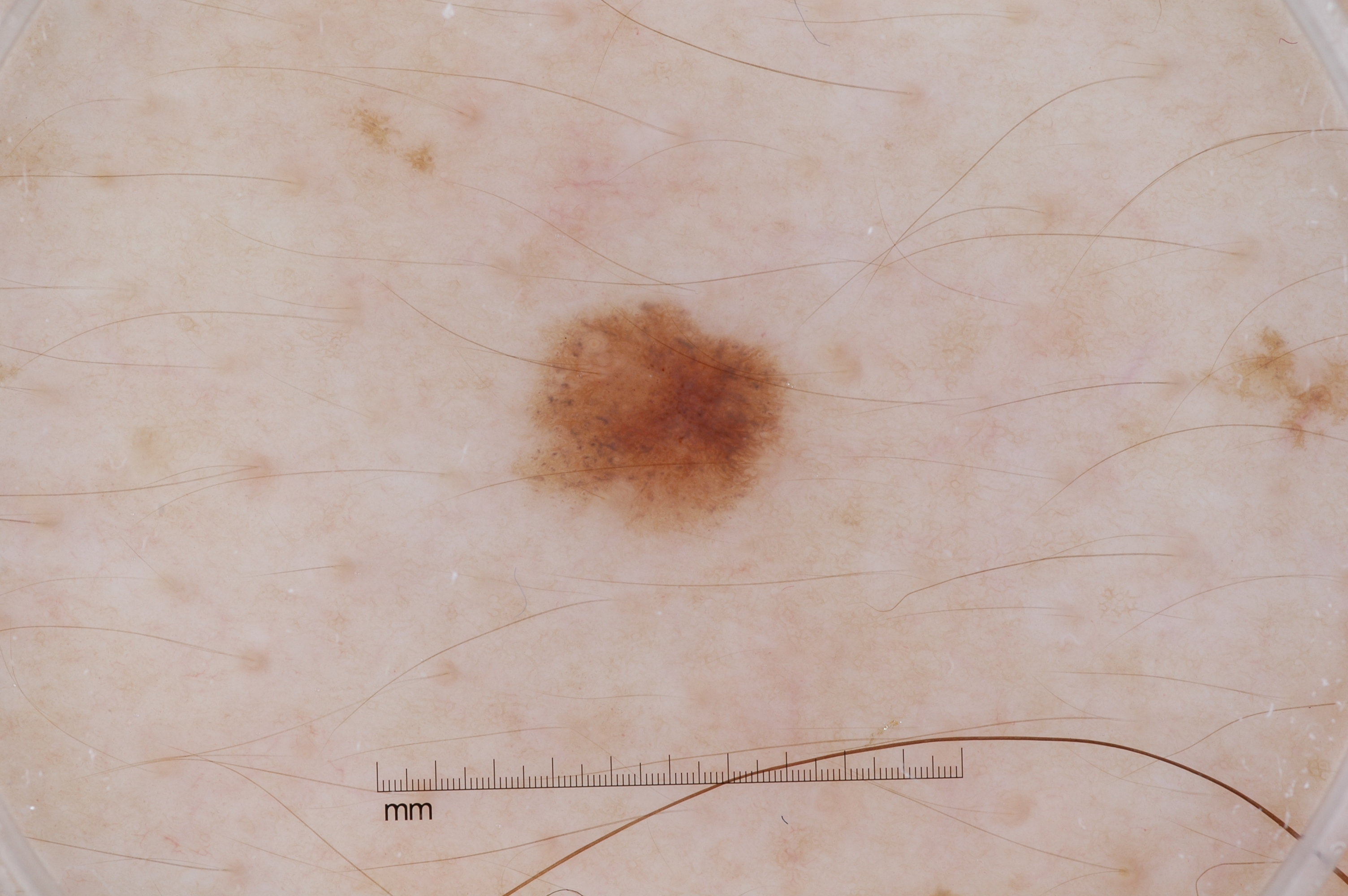Summary: A dermoscopic view of a skin lesion. On dermoscopy, the lesion shows pigment network. In (x1, y1, x2, y2) order, the lesion is located at <box>519, 299, 828, 534</box>. The lesion is small relative to the field of view. Impression: Clinically diagnosed as a melanocytic nevus, a benign lesion.